Located on the arm, back of the torso, front of the torso and head or neck. The photograph was taken at an angle — 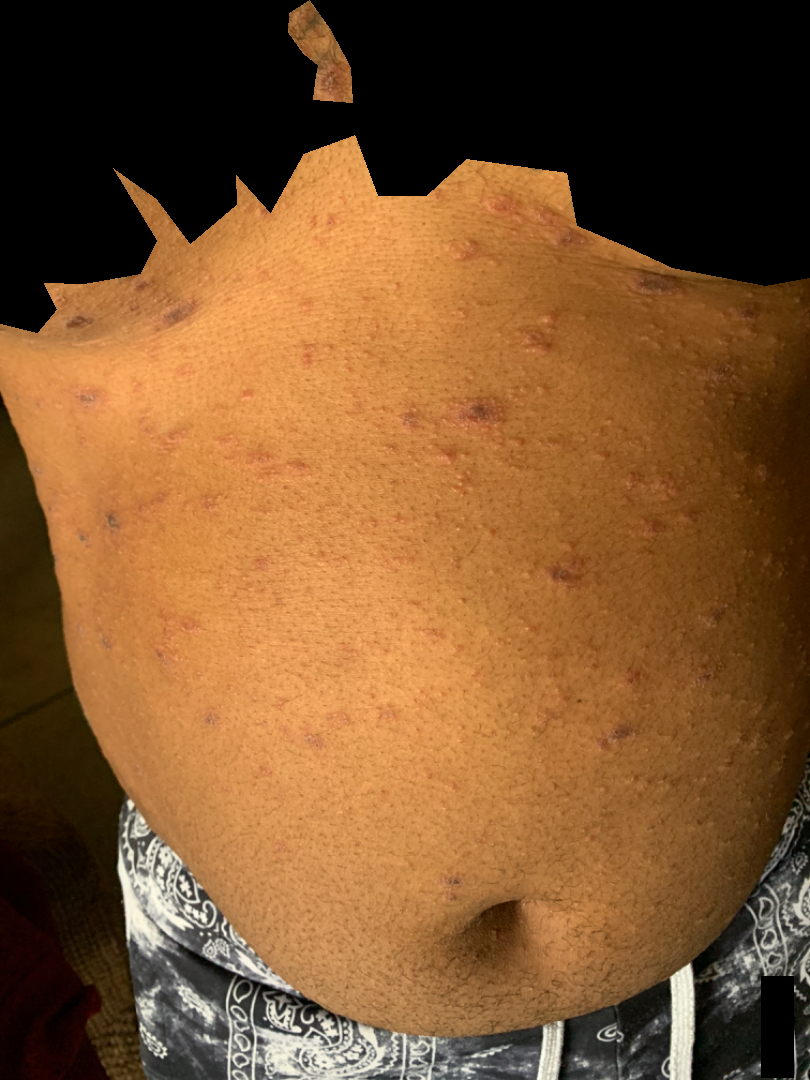• symptom duration: less than one week
• patient's own categorization: a rash
• lesion symptoms: itching
• diagnostic considerations: the leading impression is Erythema multiforme; possibly Pityriasis lichenoides; less likely is Drug Rash